Male contributor, age 30–39 · the photograph was taken at a distance: 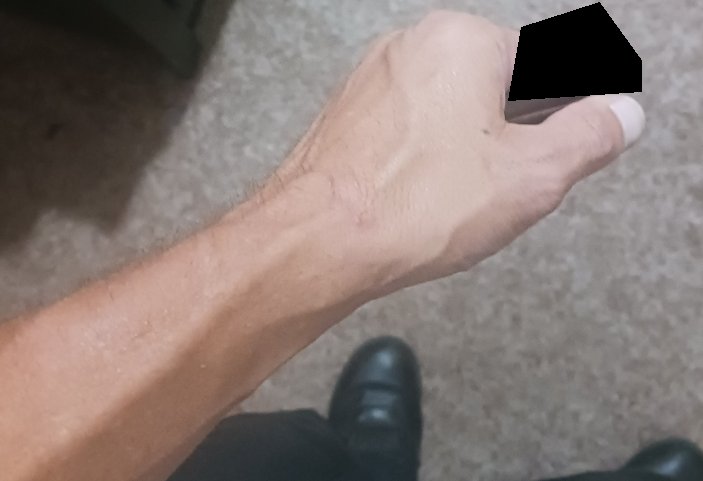In keeping with Granuloma annulare.